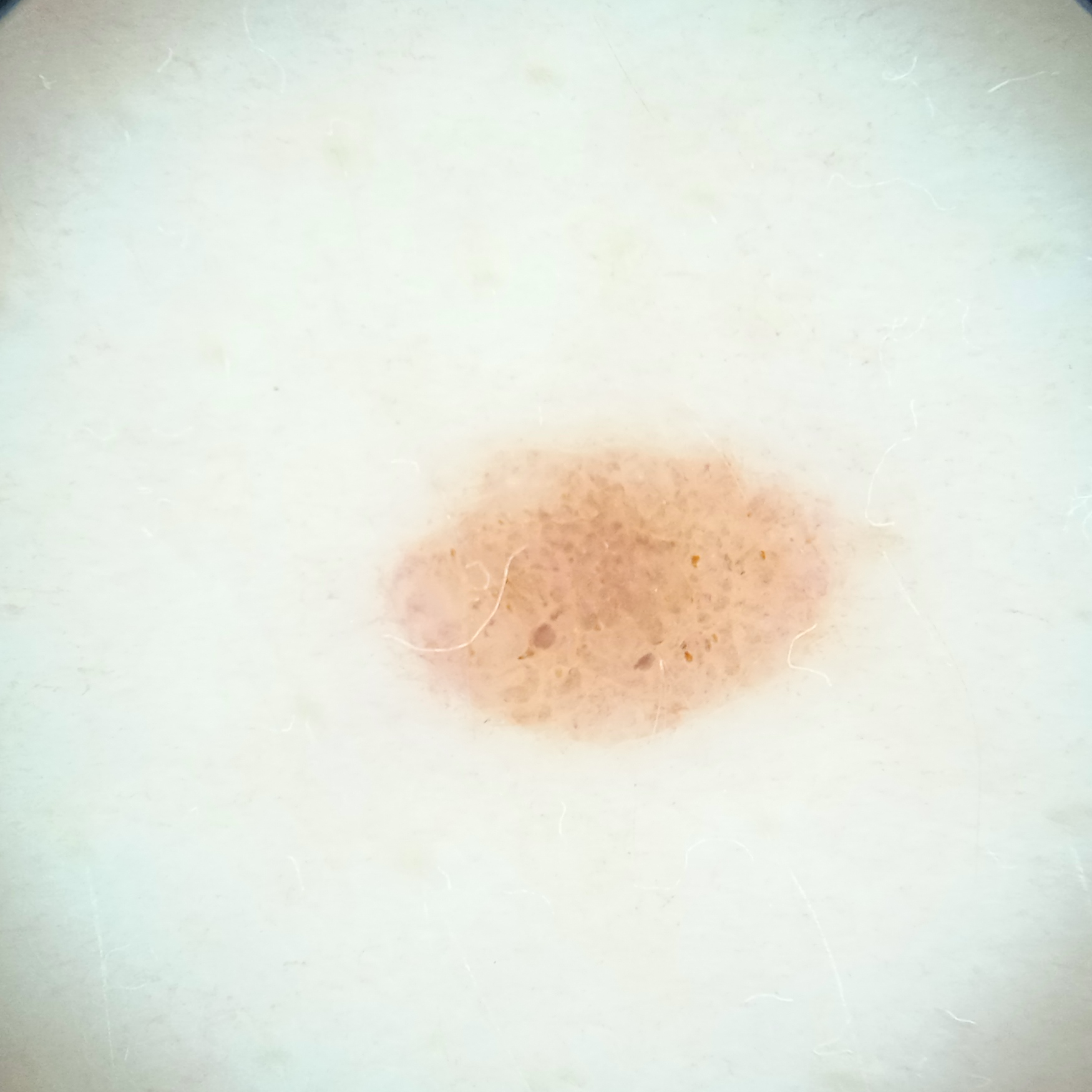Case:
* diagnosis: melanocytic nevus (dermatologist consensus)